This is a close-up image.
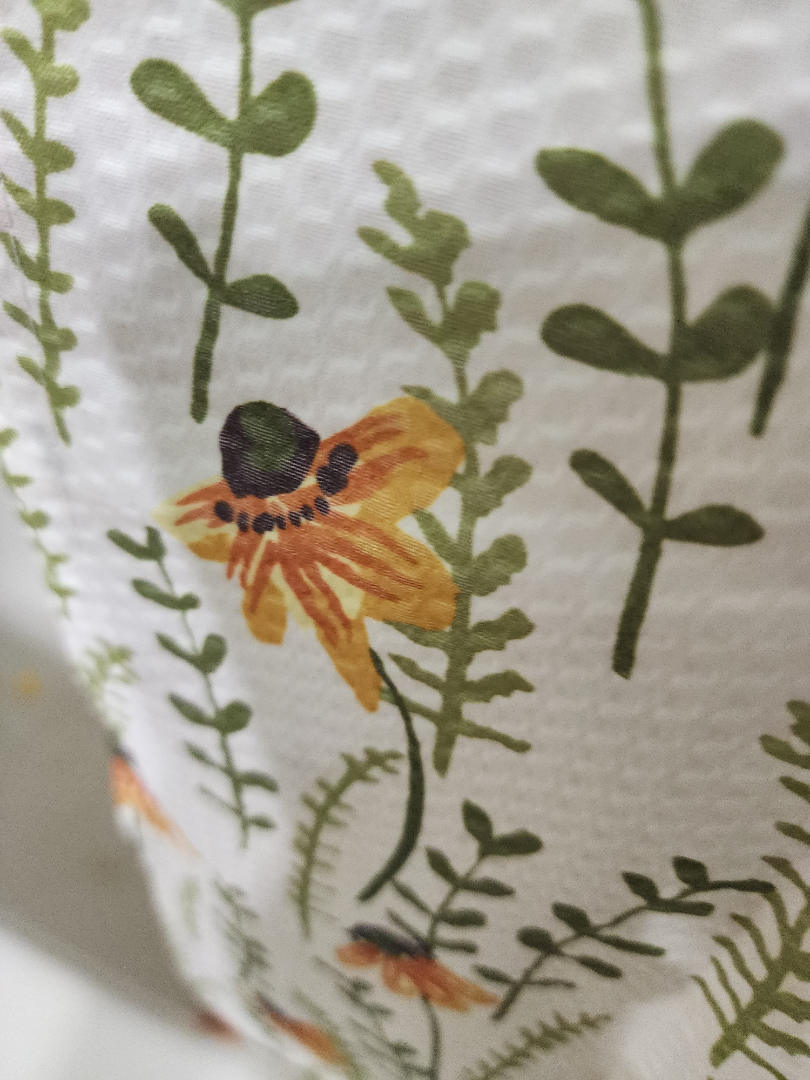Findings:
Diagnostic features were not clearly distinguishable in this photograph.